A dermoscopic view of a skin lesion, the subject is a male aged approximately 35: 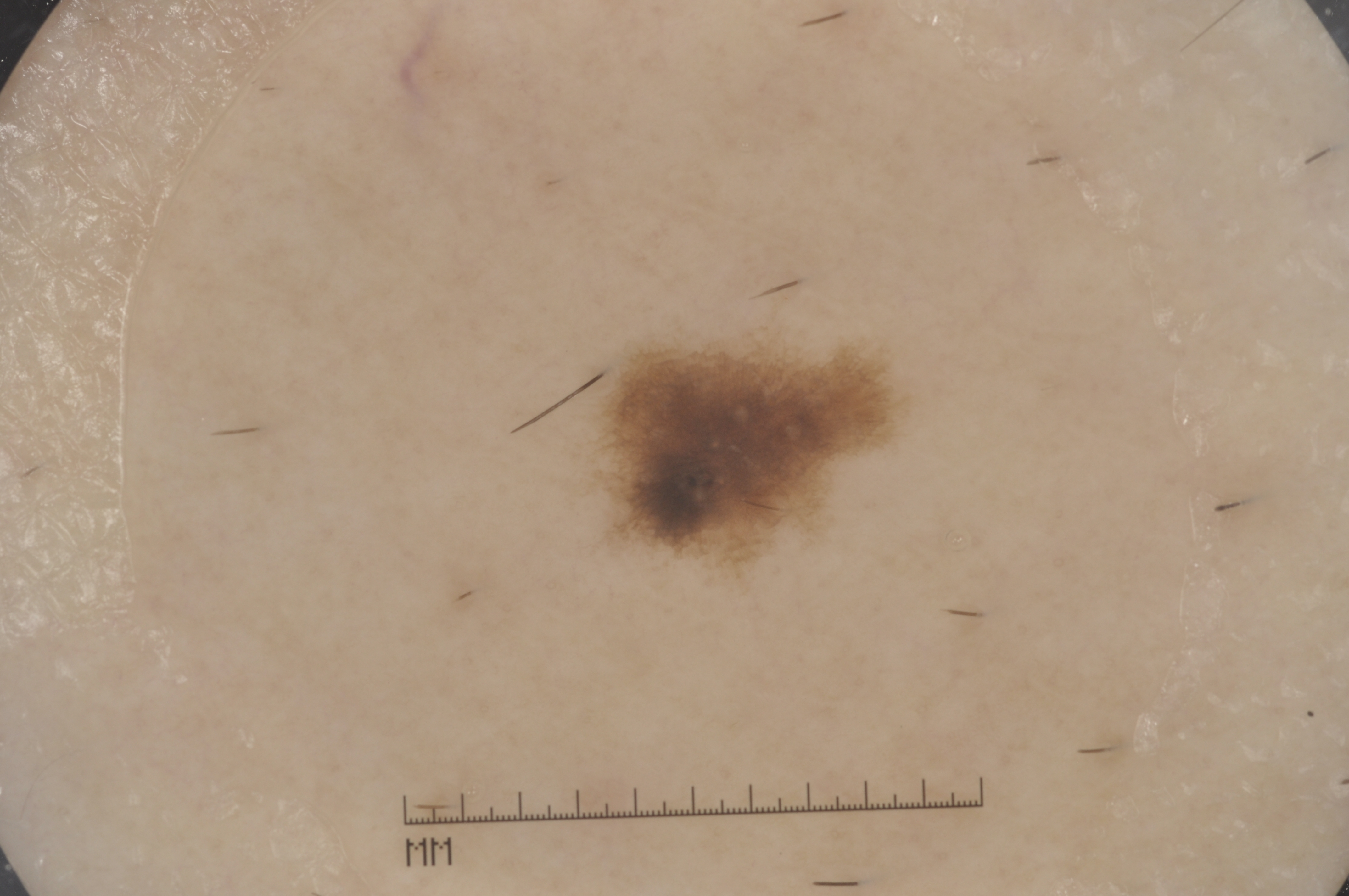As (left, top, right, bottom), the lesion occupies the region [601,343,896,560]. Dermoscopic examination shows pigment network; no milia-like cysts, streaks, or negative network. A small lesion within a wider field of skin. Clinically diagnosed as a melanocytic nevus, a benign lesion.